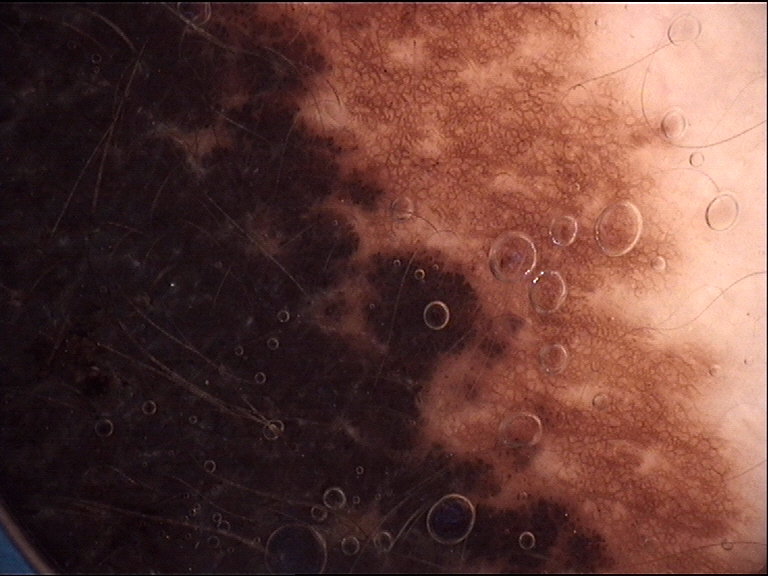image type: dermatoscopy, subtype: banal, class: congenital compound nevus (expert consensus).